A dermoscopic close-up of a skin lesion: 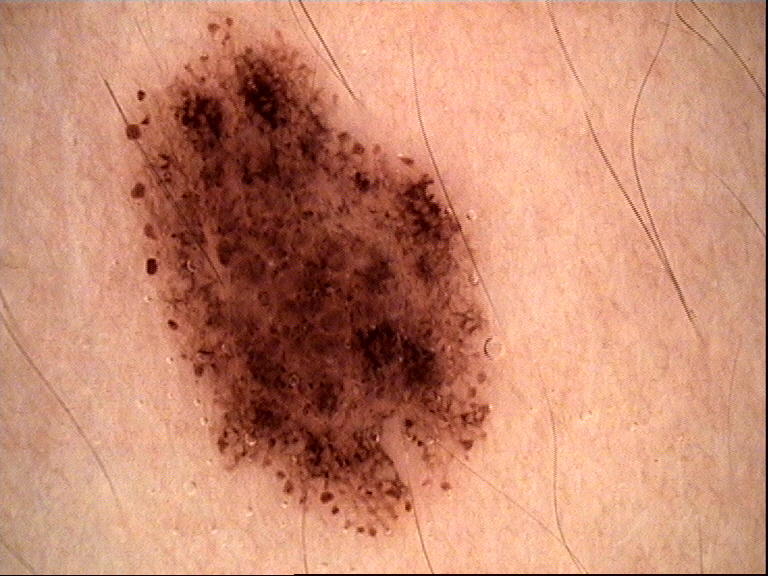Labeled as a benign lesion — a dysplastic compound nevus.